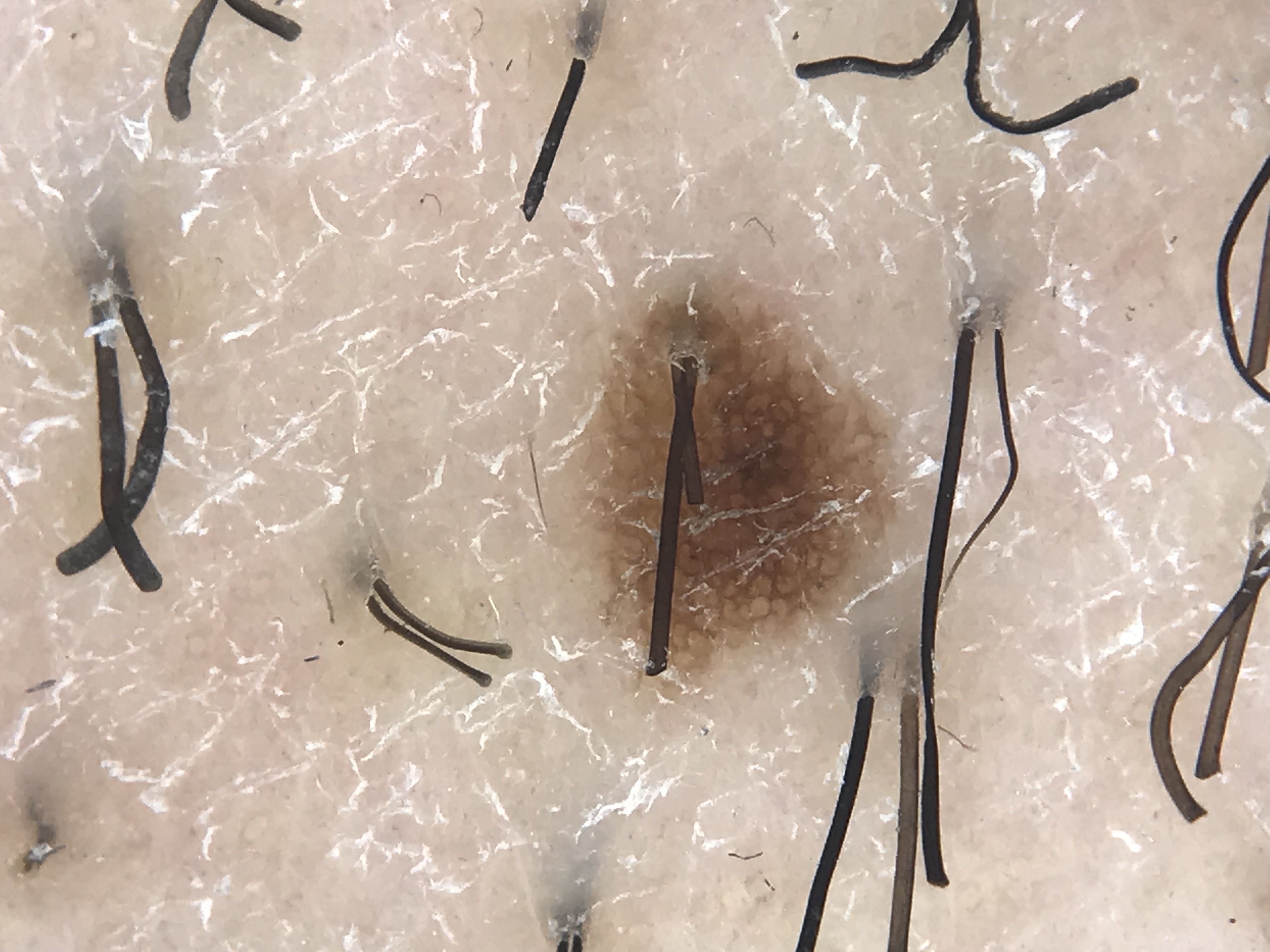<lesion>
<diagnosis>
<name>dysplastic junctional nevus</name>
<code>jd</code>
<malignancy>benign</malignancy>
<super_class>melanocytic</super_class>
<confirmation>expert consensus</confirmation>
</diagnosis>
</lesion>